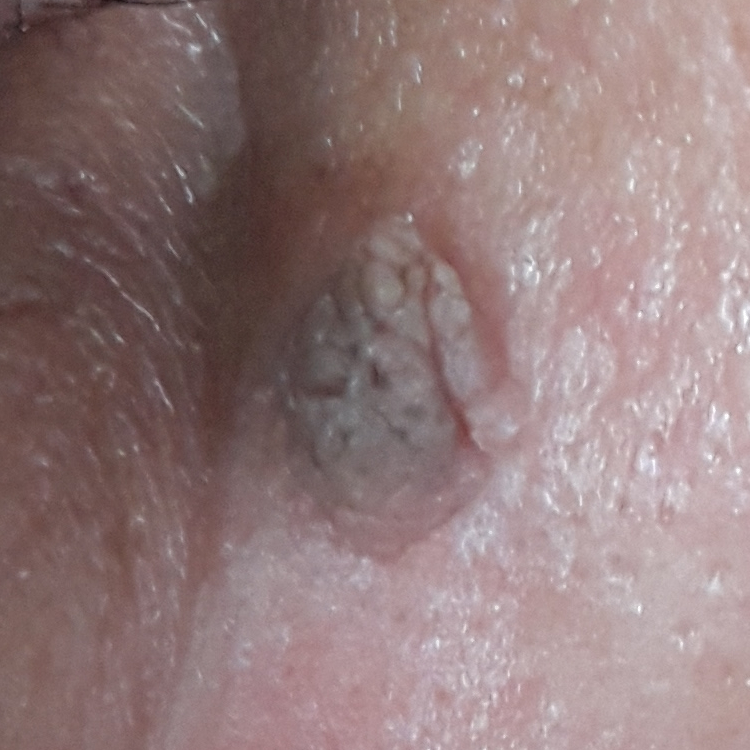| feature | finding |
|---|---|
| subject | aged 45 |
| image | smartphone clinical photo |
| anatomic site | the nose |
| symptoms | growth, elevation |
| diagnosis | seborrheic keratosis (clinical consensus) |